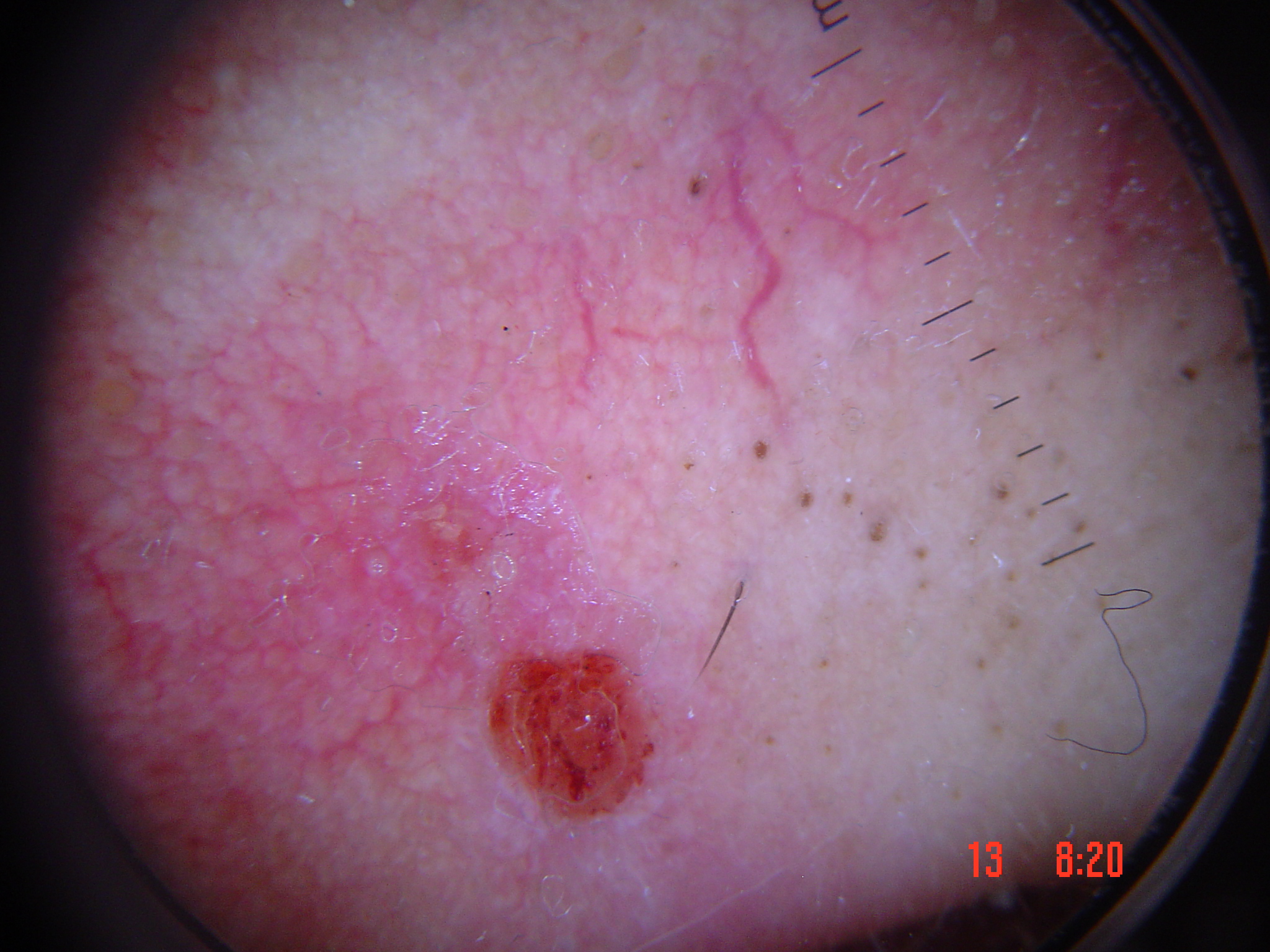subtype: keratinocytic
diagnosis: squamous cell carcinoma (biopsy-proven)